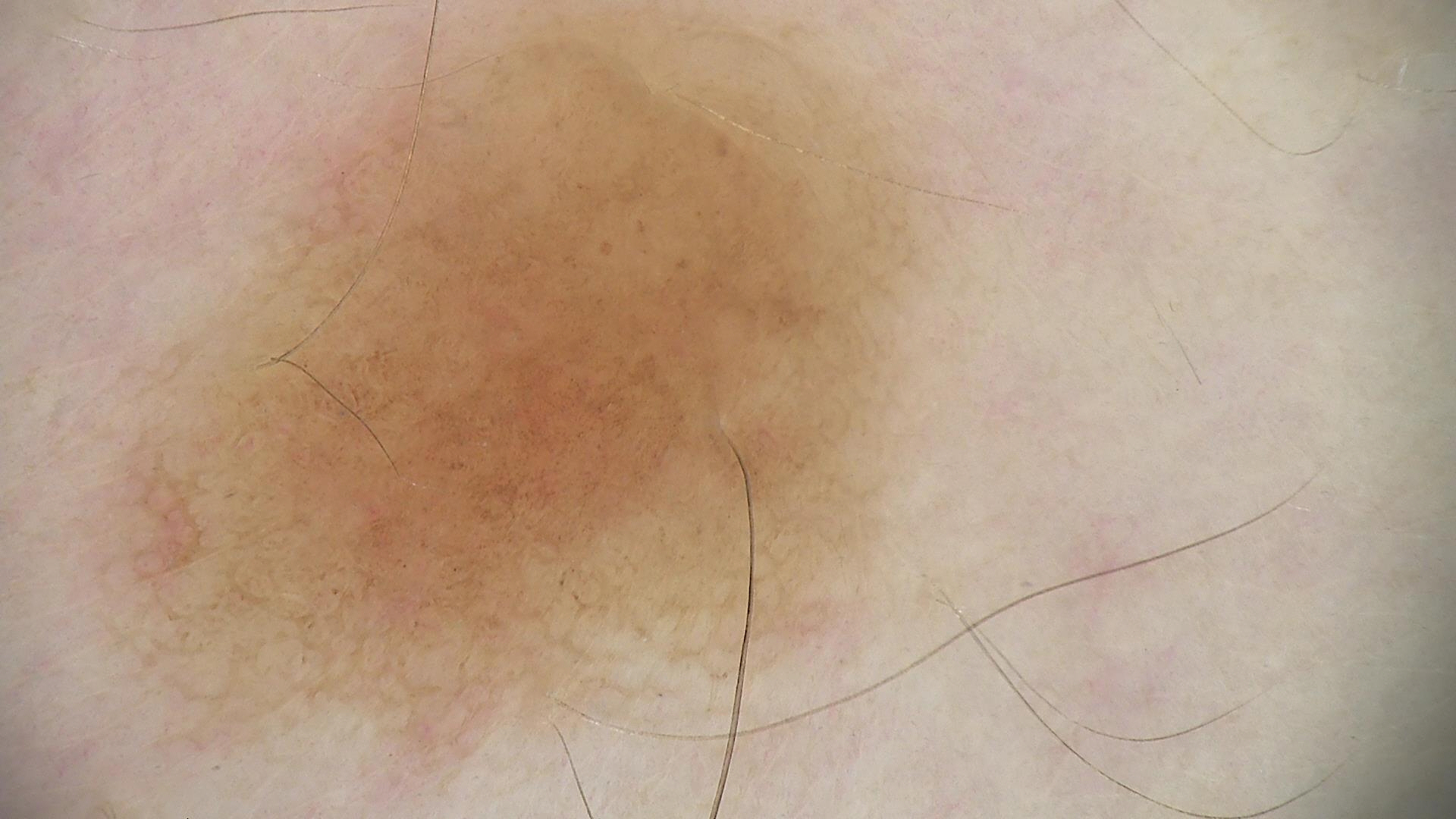Conclusion: Consistent with a compound nevus.